A dermoscopic image of a skin lesion.
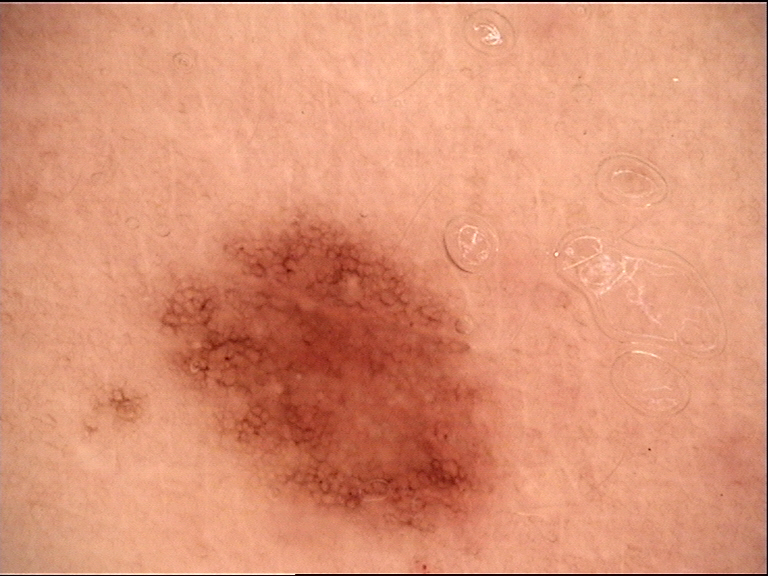Impression: Labeled as a benign lesion — a dysplastic junctional nevus.